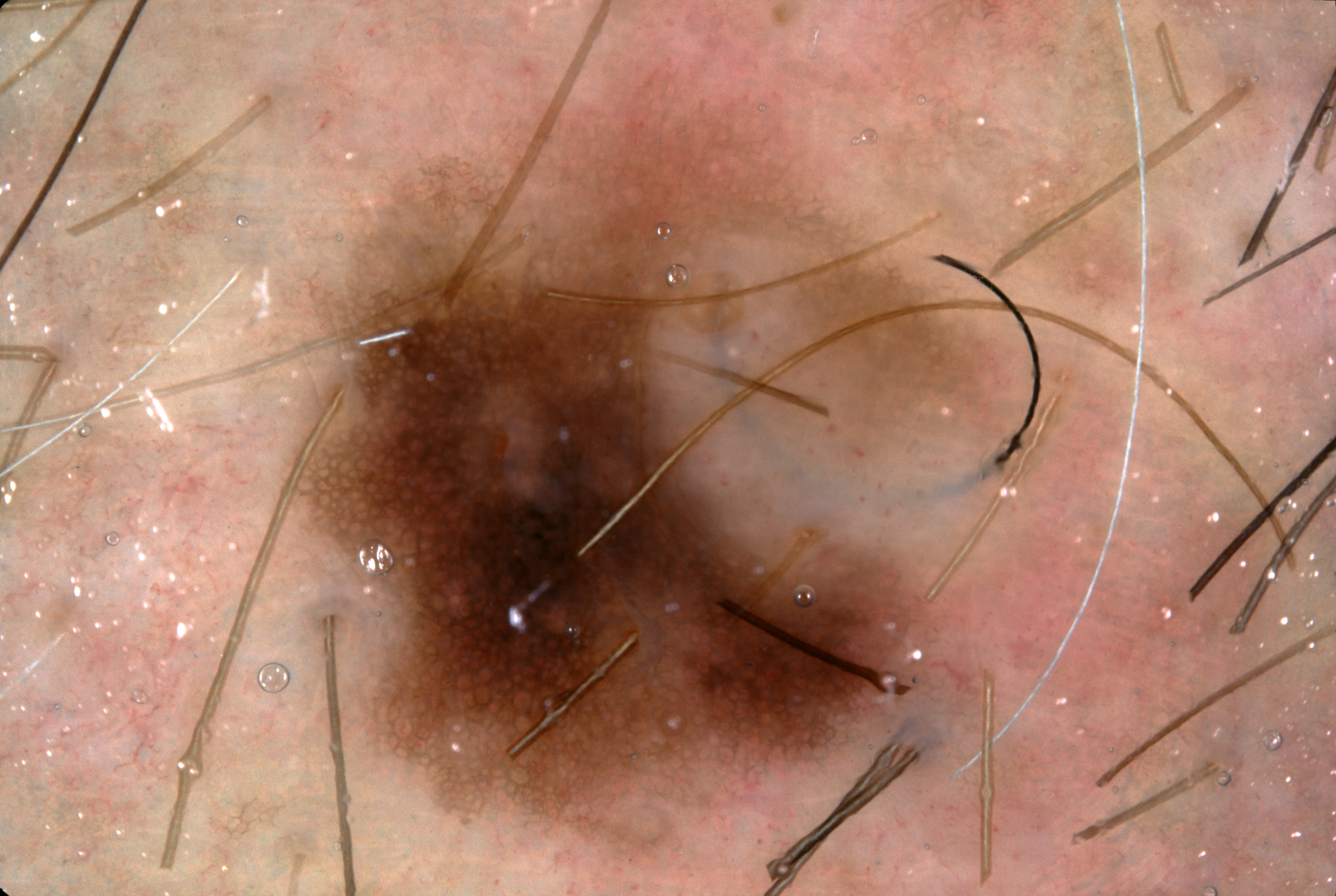Summary:
Dermoscopy of a skin lesion. The subject is a male aged around 50. The lesion takes up about 28% of the image. The lesion occupies the region left=303, top=105, right=960, bottom=826. The dermoscopic pattern shows pigment network; no negative network, milia-like cysts, or streaks.
Impression:
The lesion was assessed as a melanocytic nevus.